FST I, the subject is a female aged 18–29, a close-up photograph, reported duration is three to twelve months, the patient indicates bothersome appearance:
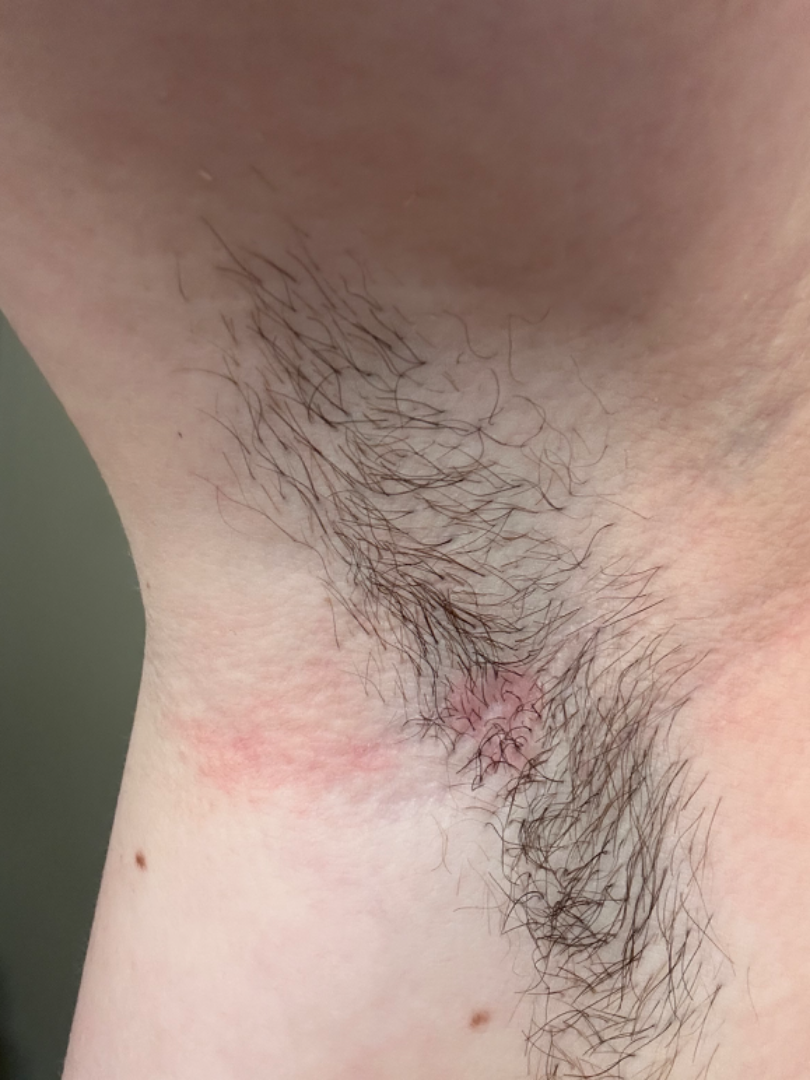differential = Intertrigo and Irritant Contact Dermatitis were considered with similar weight; less likely is Candida intertrigo